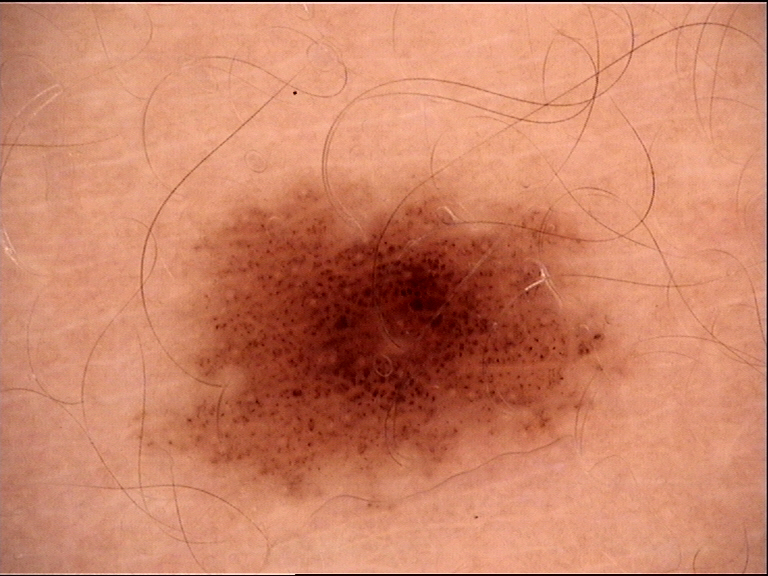A skin lesion imaged with a dermatoscope. This is a banal lesion. The diagnosis was a junctional nevus.